The affected area is the head or neck and front of the torso; female contributor, age 18–29; close-up view:
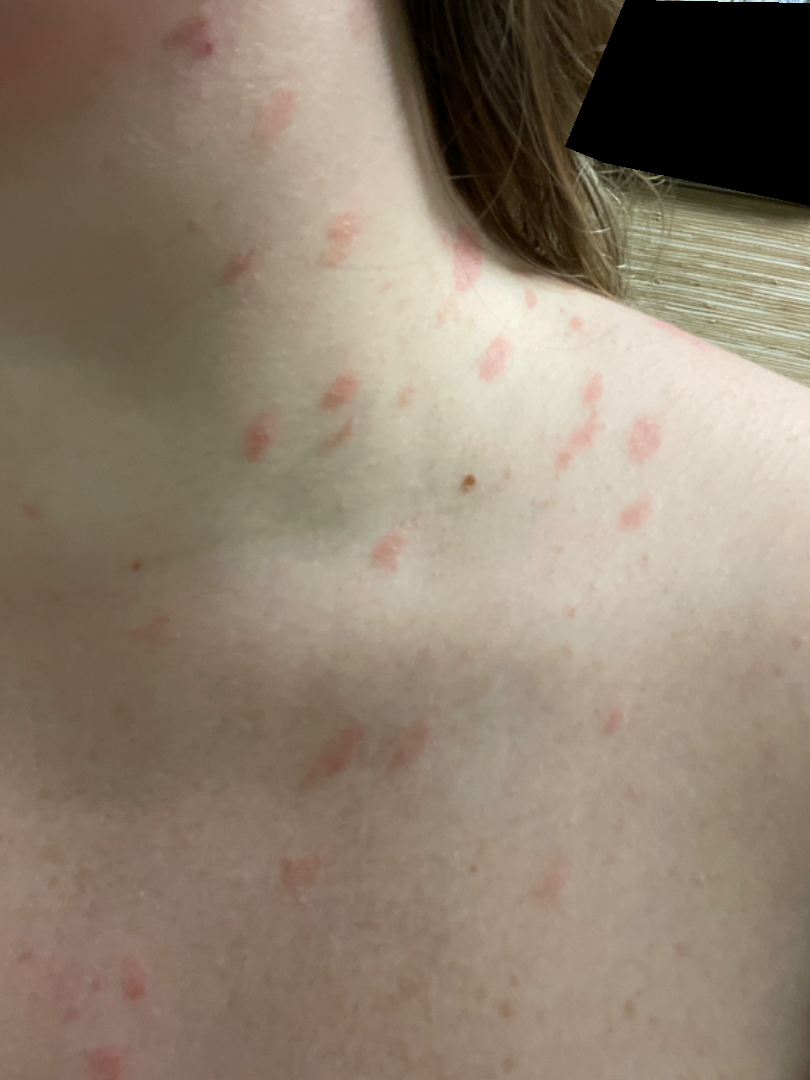assessment — most likely Pityriasis rosea; also consider Psoriasis